A skin lesion imaged with a dermatoscope:
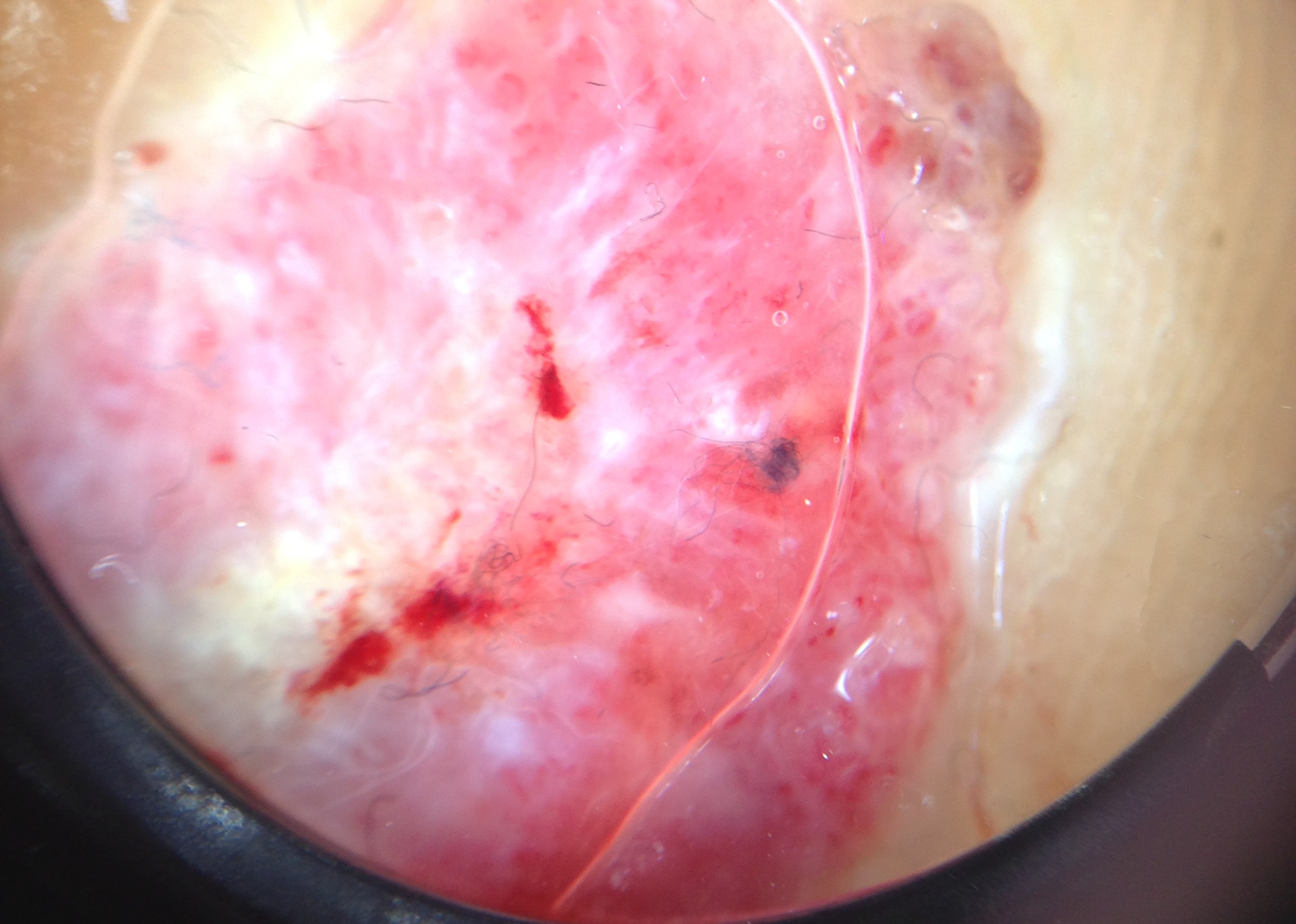Findings:
– class: acral nodular melanoma (biopsy-proven)